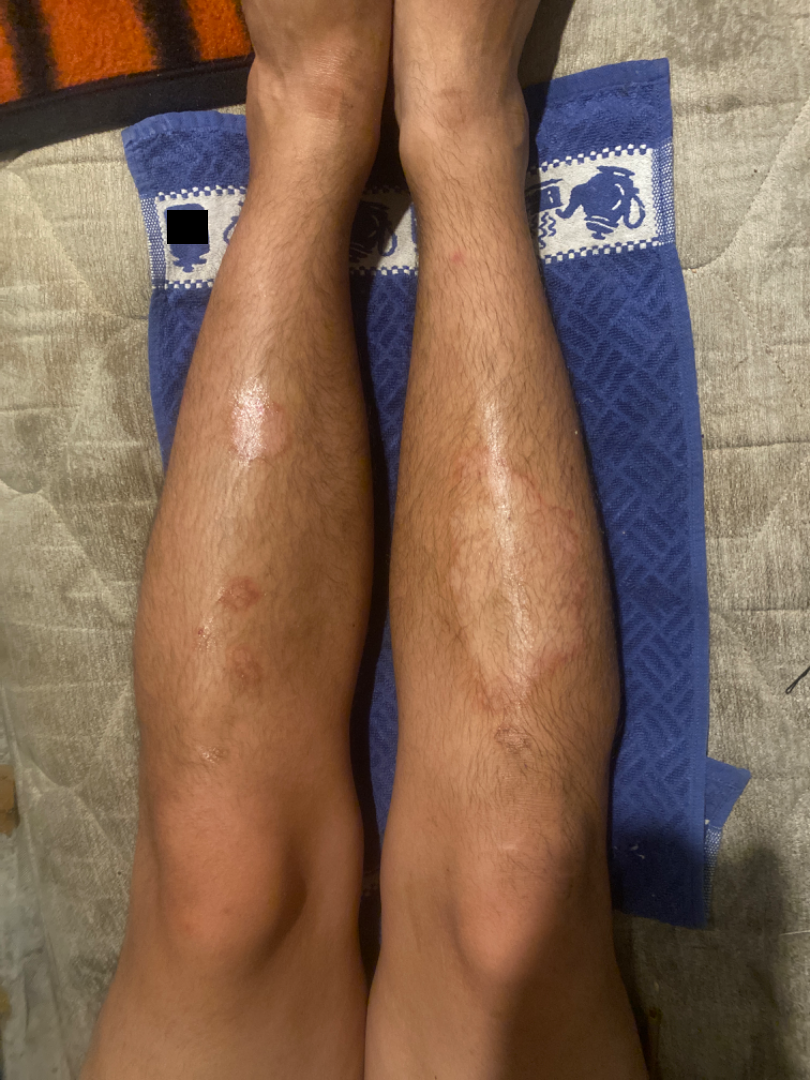{"differential": {"leading": ["Necrobiosis lipoidica"], "considered": ["Tinea", "Porokeratosis"], "unlikely": ["Eczema", "Lichen sclerosus"]}}